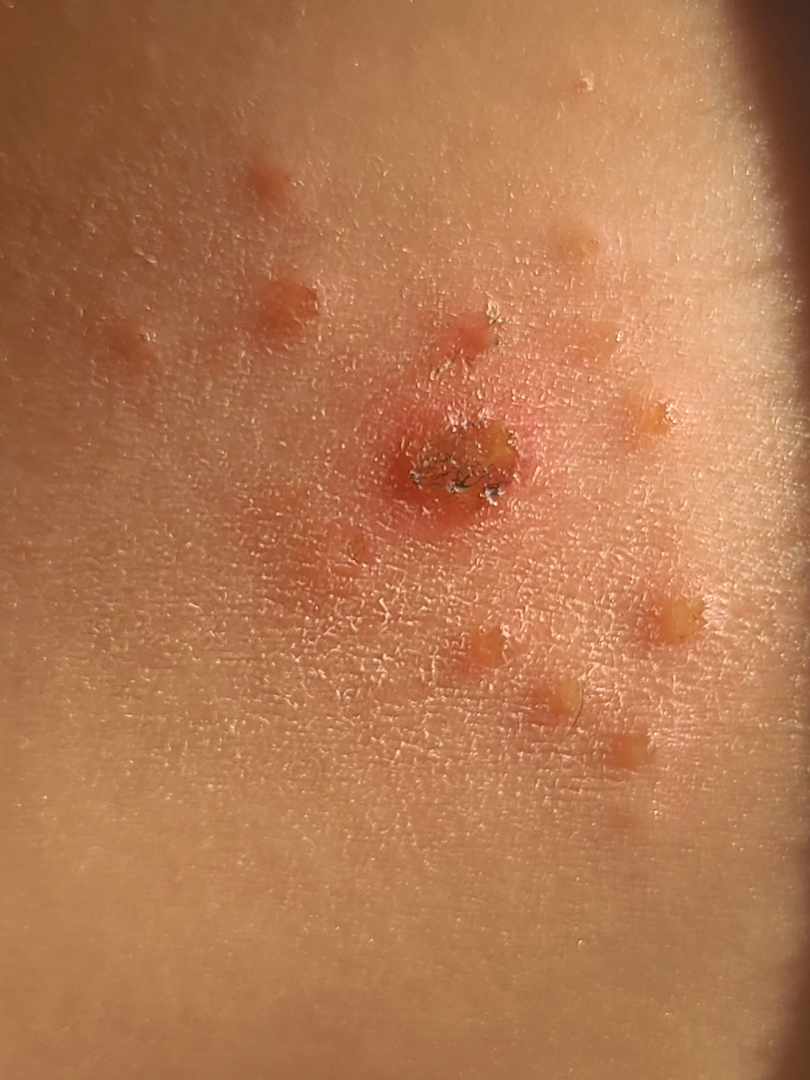Review: The image was not sufficient for the reviewer to characterize the skin condition. Patient information: Symptoms reported: enlargement, bothersome appearance, burning, pain and itching. The patient described the issue as a rash. Located on the leg. Texture is reported as raised or bumpy and fluid-filled. This image was taken at an angle. The patient indicates the condition has been present for less than one week.